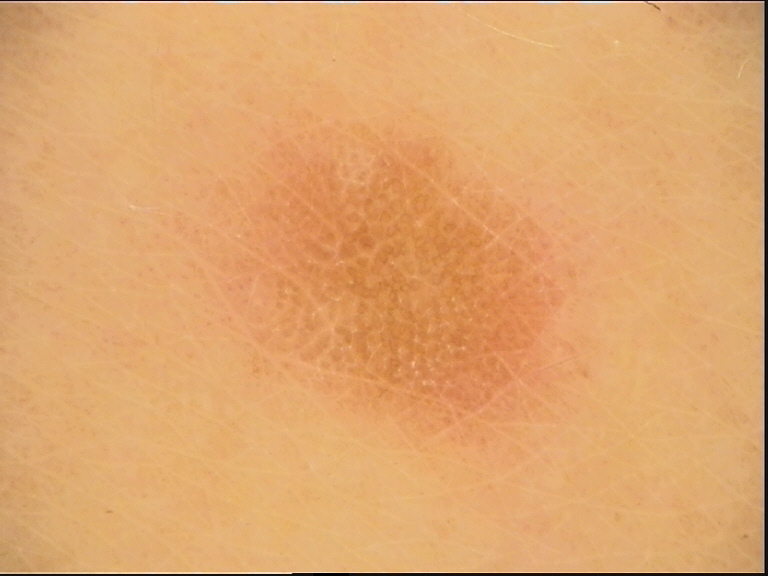imaging=dermoscopy
class=seborrheic keratosis (expert consensus)